A dermoscopic photograph of a skin lesion: 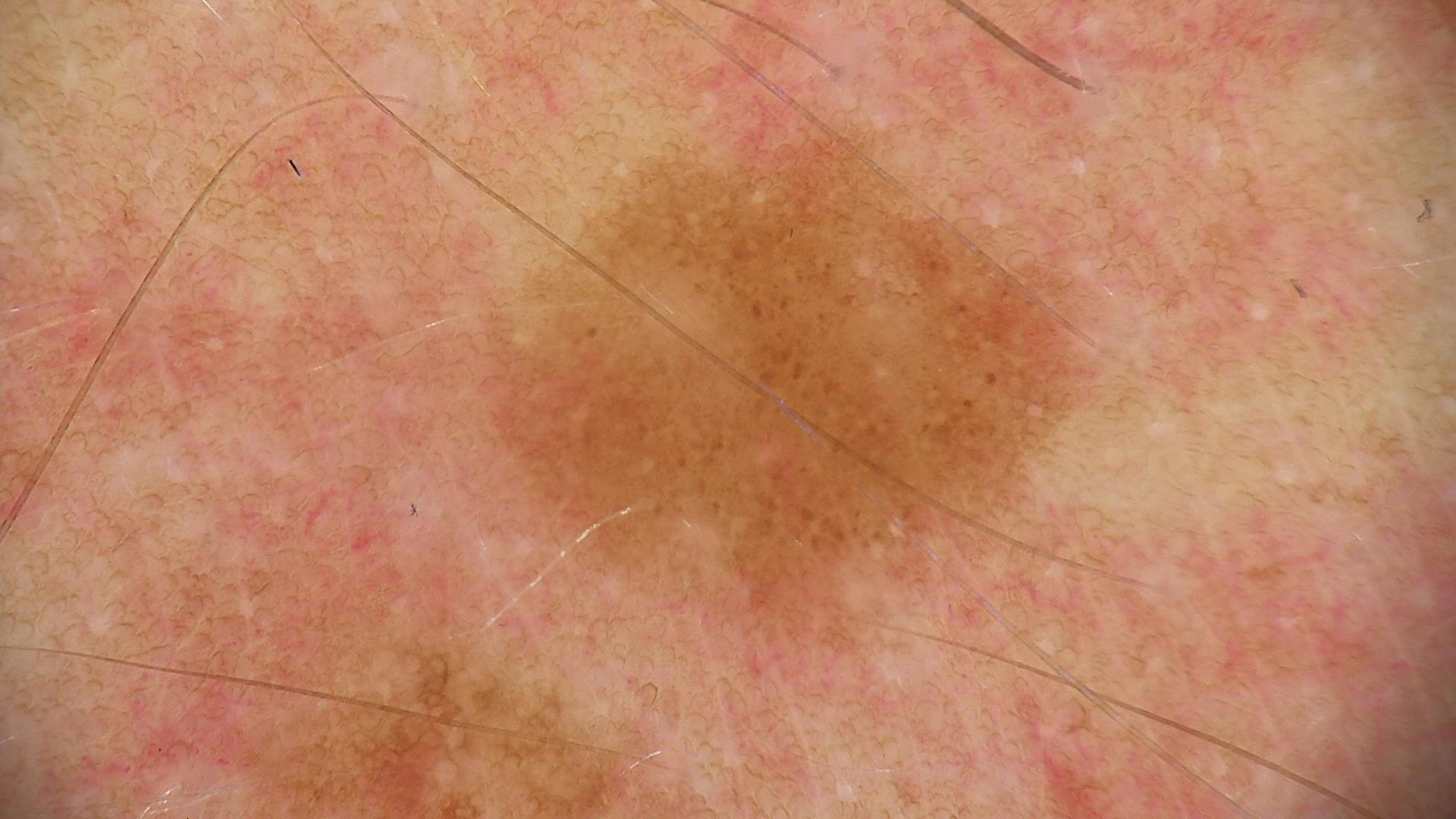The diagnosis was a benign lesion — a dysplastic junctional nevus.